Located on the head or neck; an image taken at a distance.
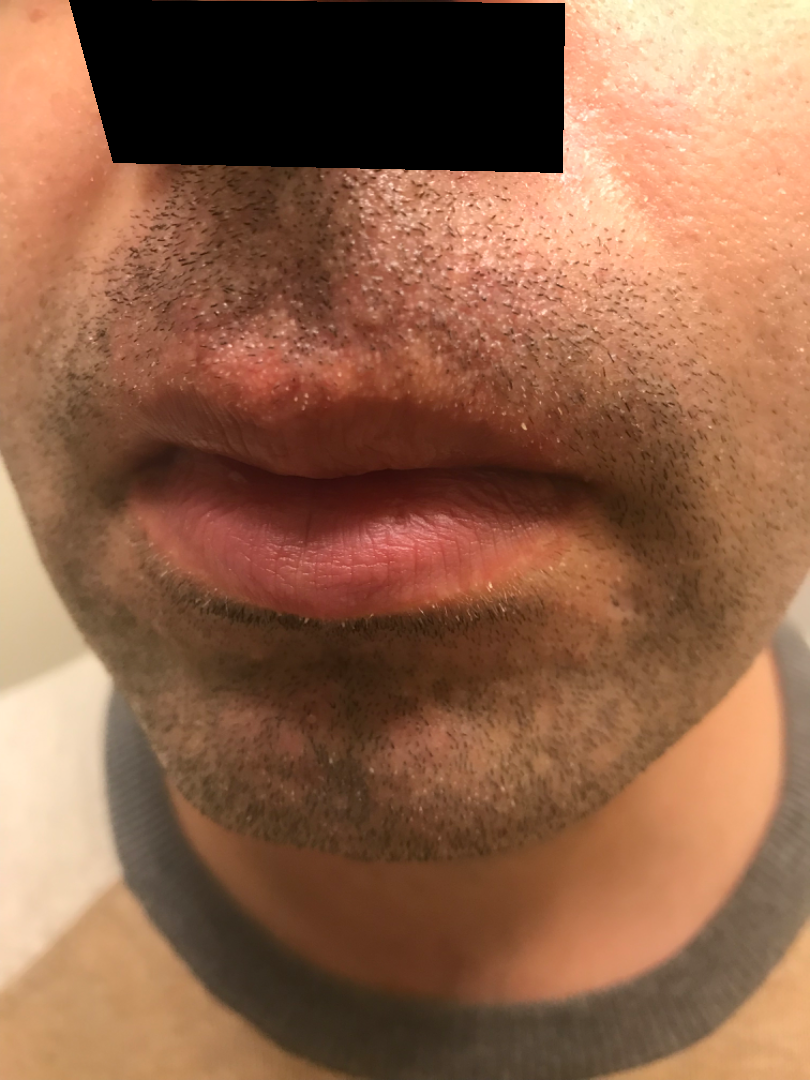The reviewer was unable to grade this case for skin condition.